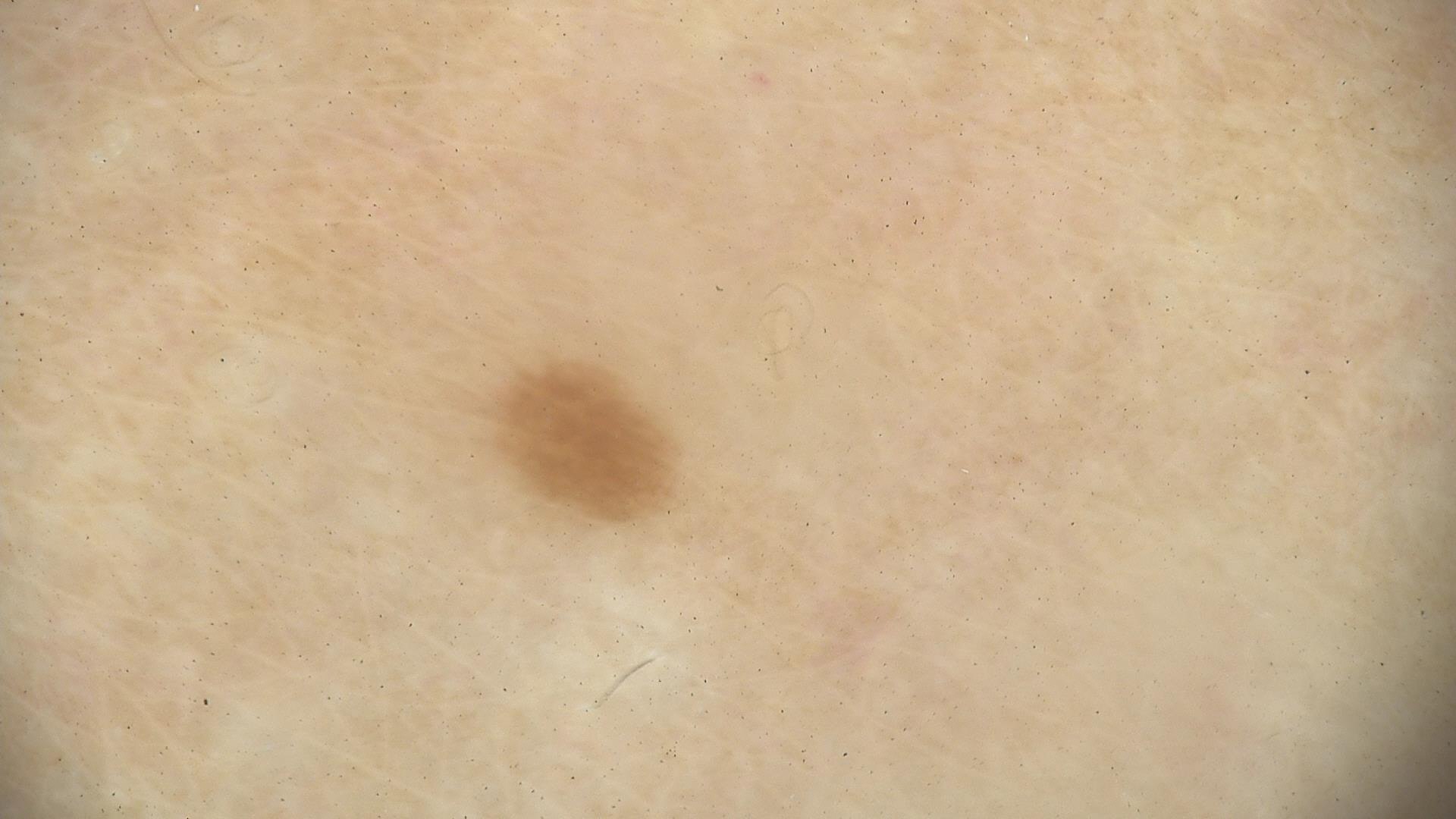{
  "image": "dermatoscopy",
  "diagnosis": {
    "name": "dysplastic junctional nevus",
    "code": "jd",
    "malignancy": "benign",
    "super_class": "melanocytic",
    "confirmation": "expert consensus"
  }
}